This is a close-up image: 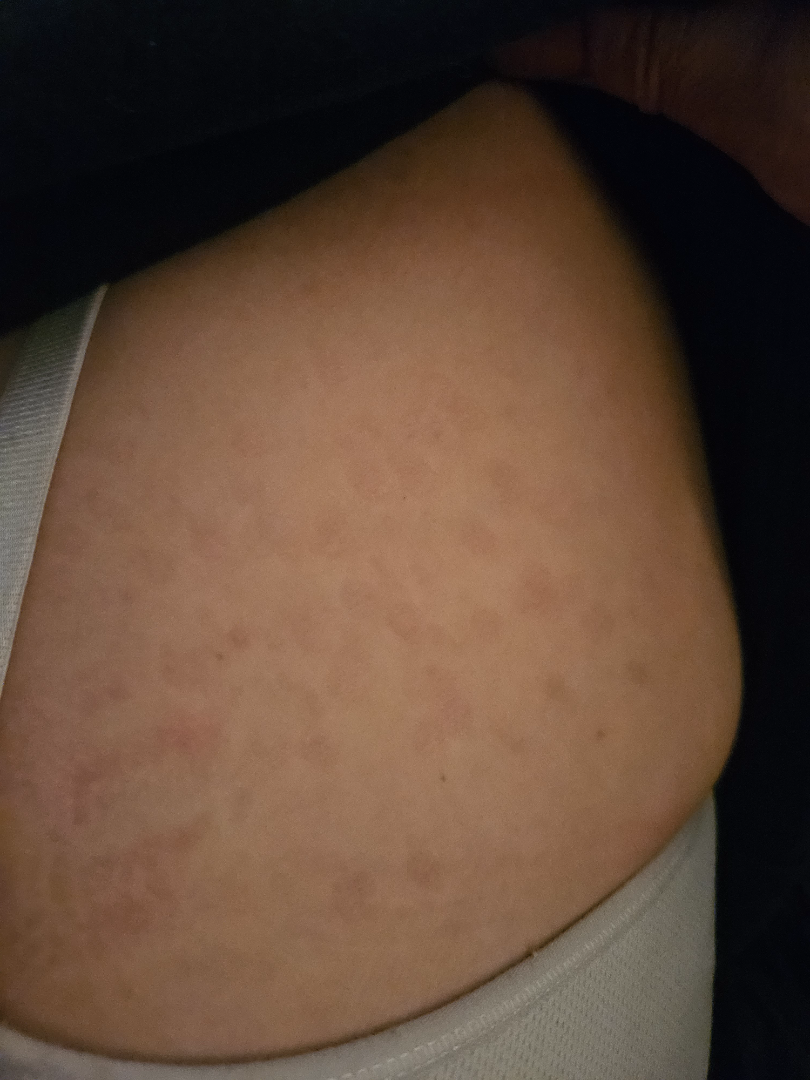| field | value |
|---|---|
| differential | Tinea Versicolor (67%); Post-Inflammatory hyperpigmentation (33%) |